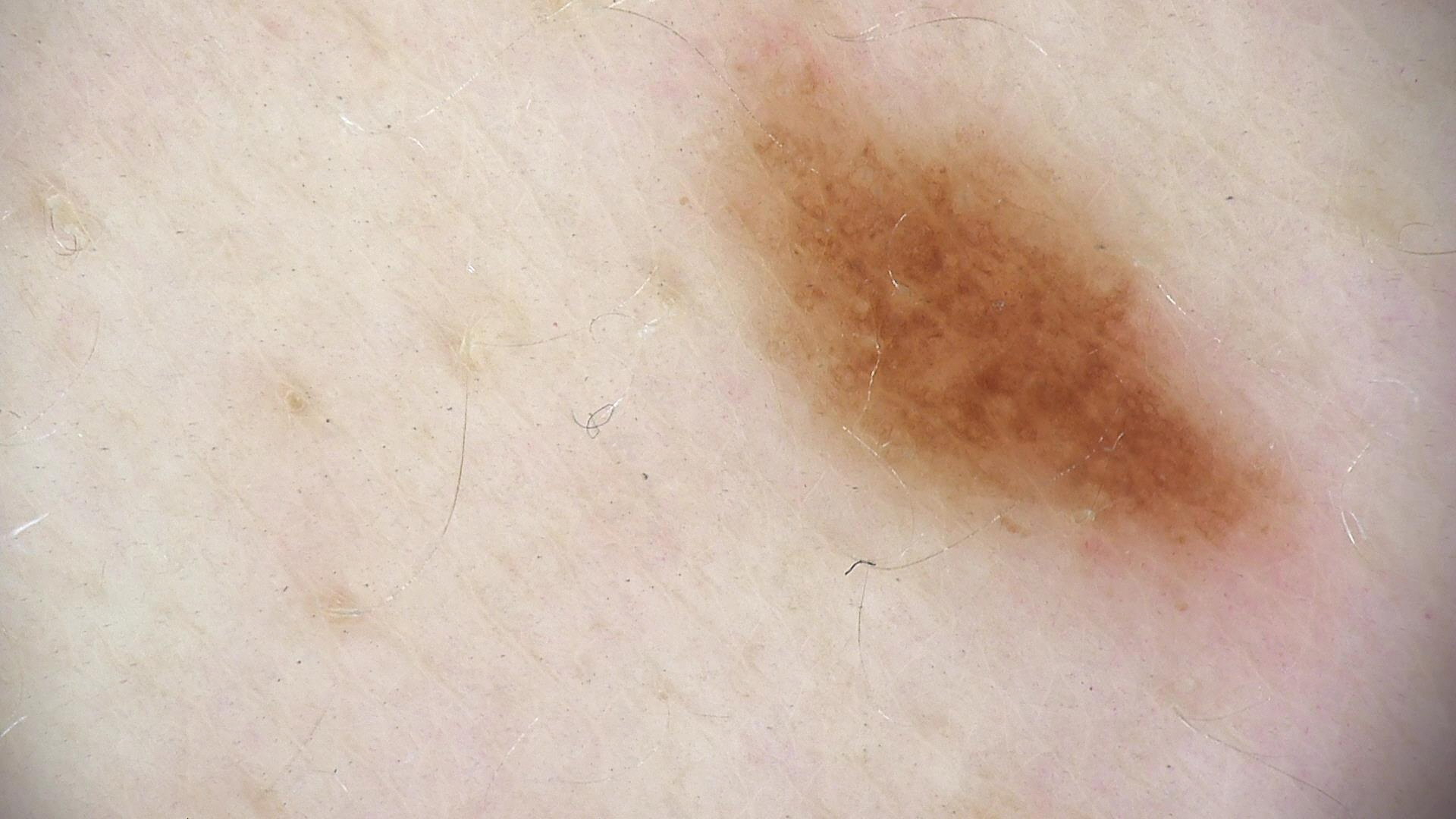modality: dermatoscopy
diagnostic label: dysplastic junctional nevus (expert consensus)